The photograph was taken at an angle · the affected area is the head or neck, front of the torso, arm, back of the torso and back of the hand: 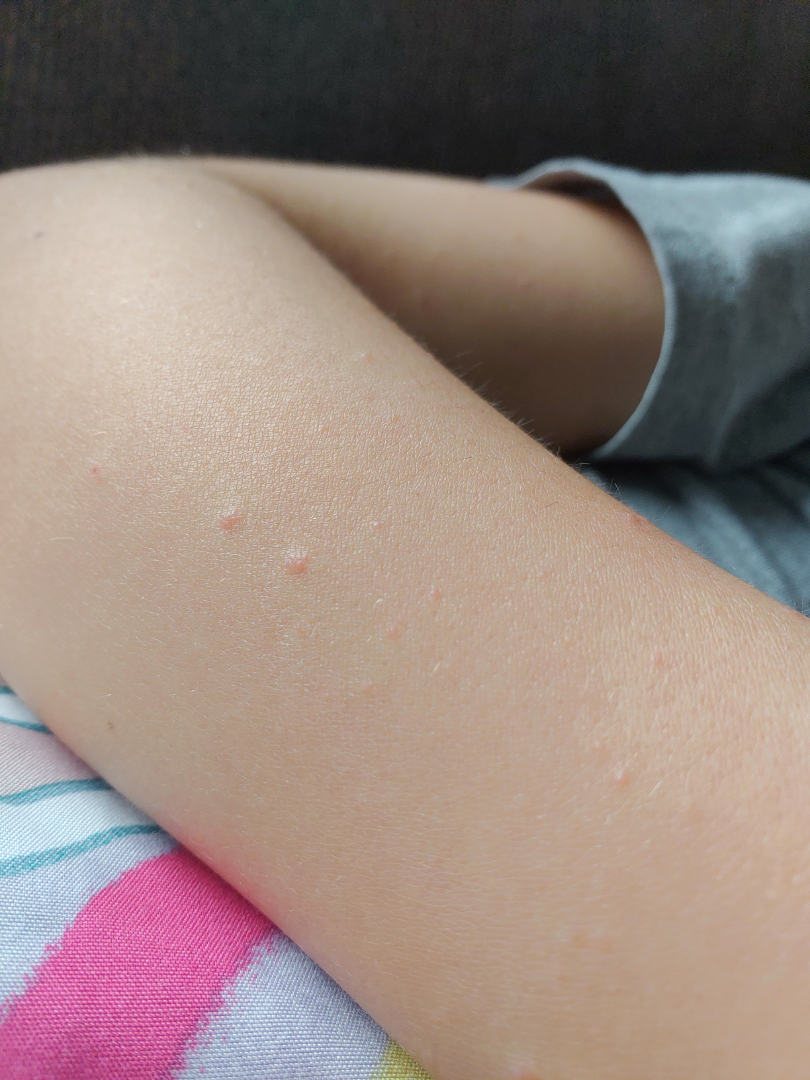Q: What was the assessment?
A: unable to determine